A dermoscopic photograph of a skin lesion.
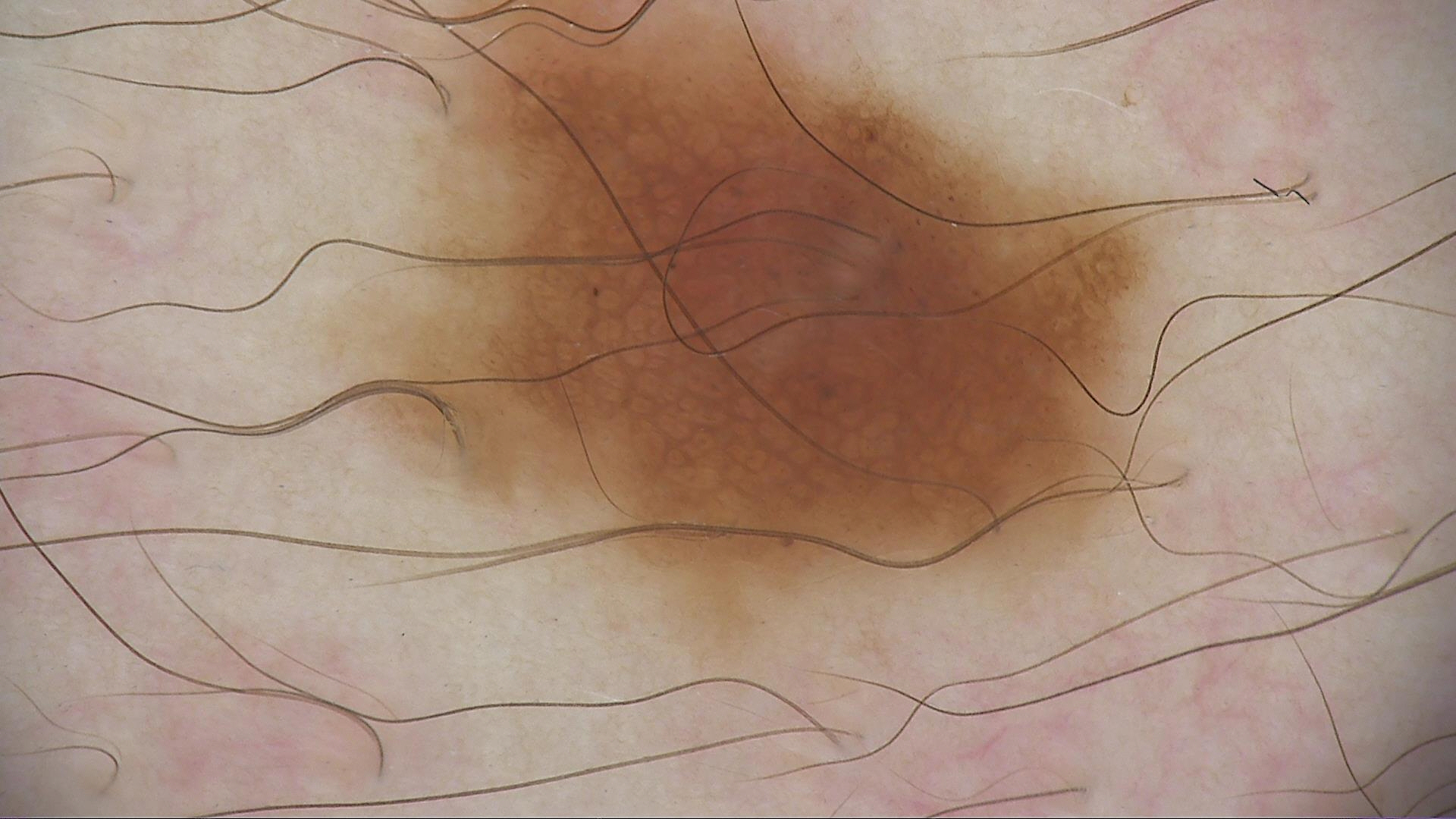Classified as a benign lesion — a dysplastic junctional nevus.